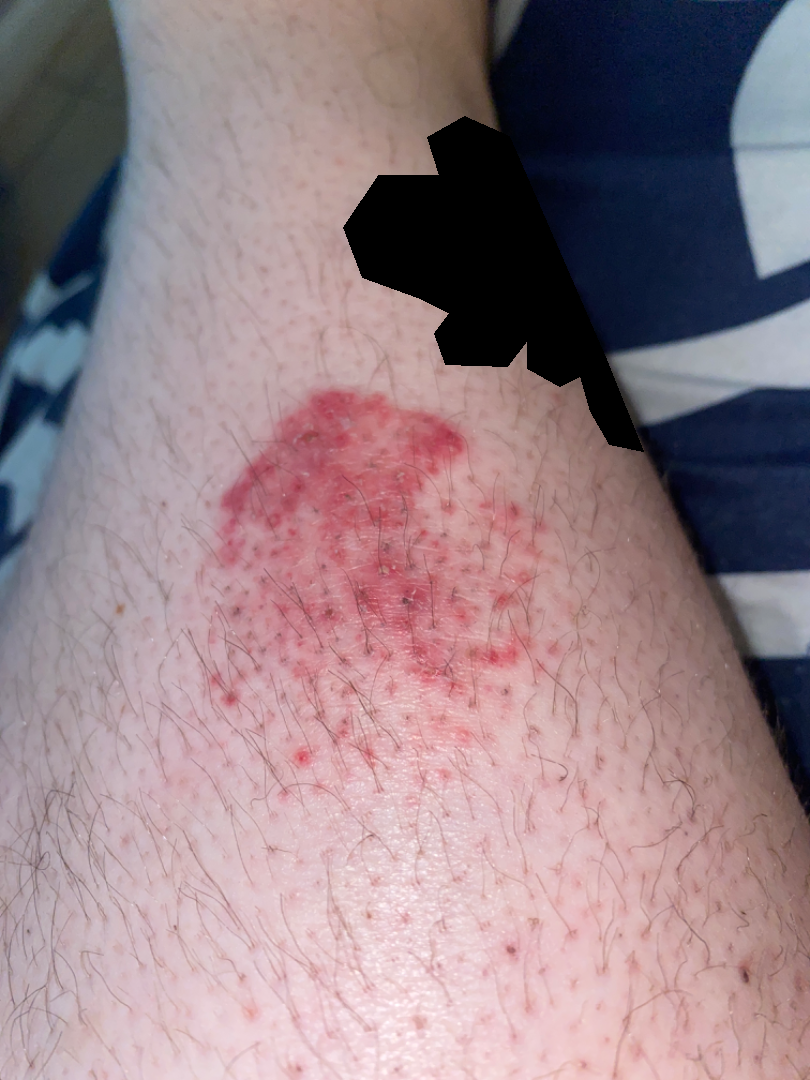Located on the head or neck and leg. This is a close-up image. Female patient, age 18–29. On remote review of the image, the impression is Acute dermatitis, NOS.